Texture is reported as raised or bumpy, symptoms reported: itching, a close-up photograph, the leg and front of the torso are involved, no associated systemic symptoms reported, reported duration is one to three months: 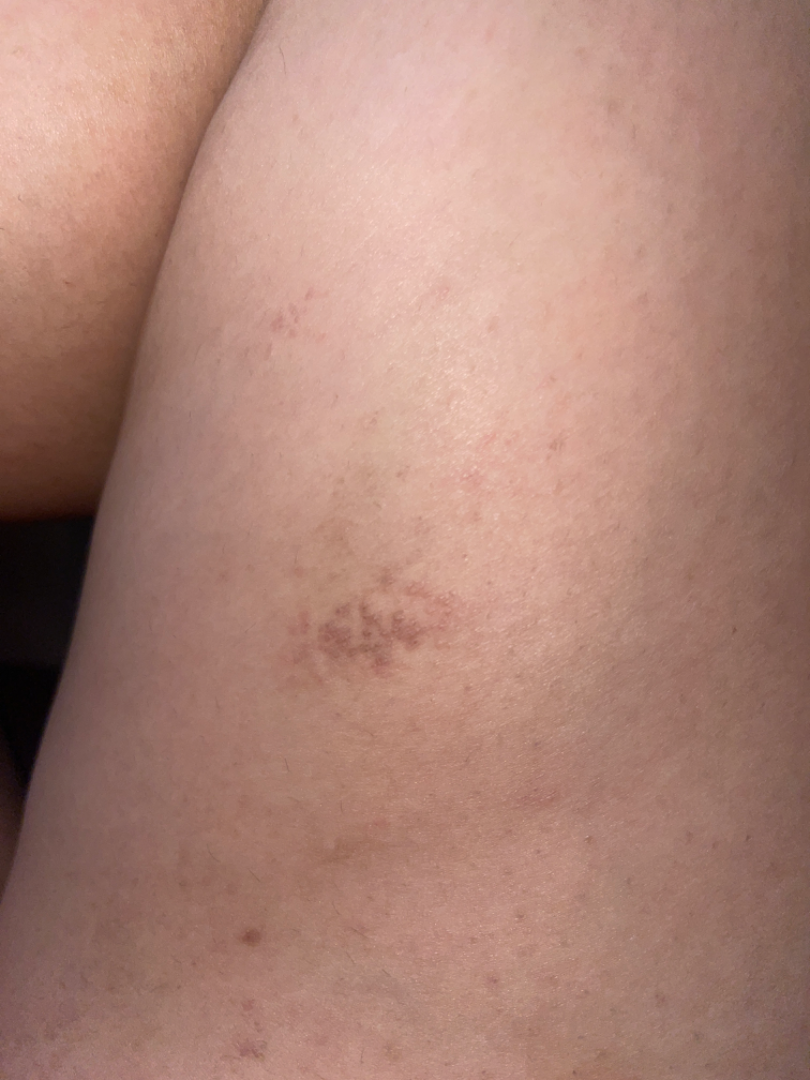The reviewing clinician's impression was: most likely Eczema; also consider Epidermal nevus; possibly Milia.